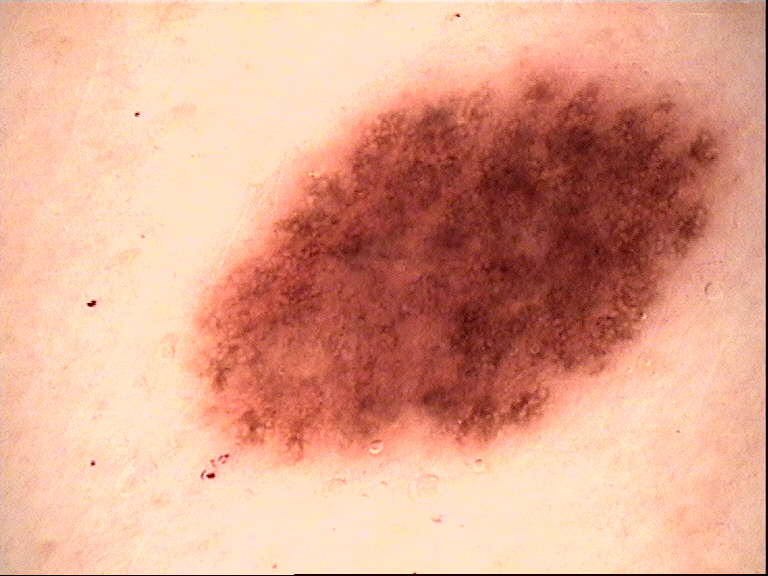Classified as a dysplastic compound nevus.